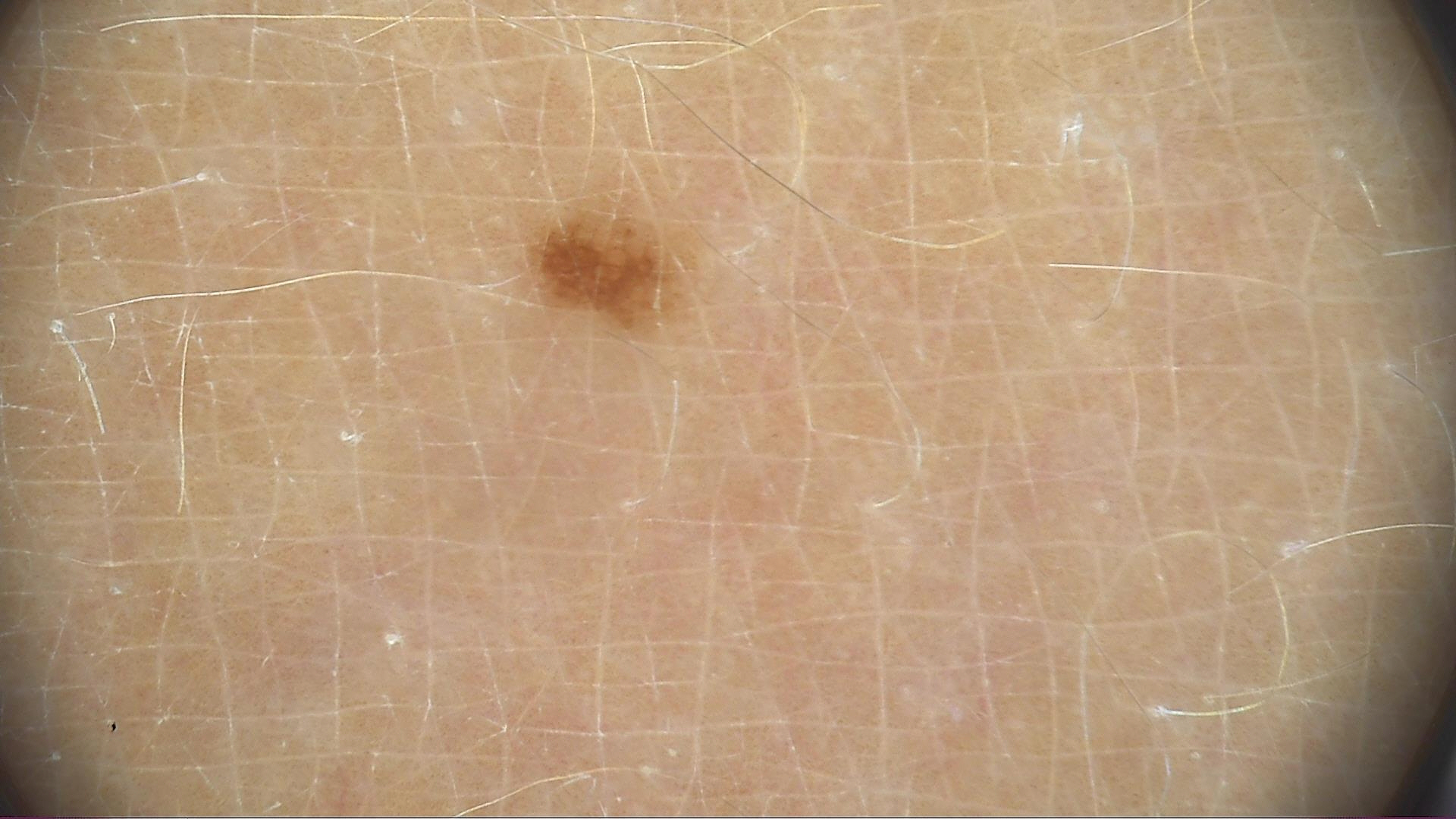Case:
A dermoscopic close-up of a skin lesion.
Impression:
The diagnostic label was a banal lesion — a junctional nevus.